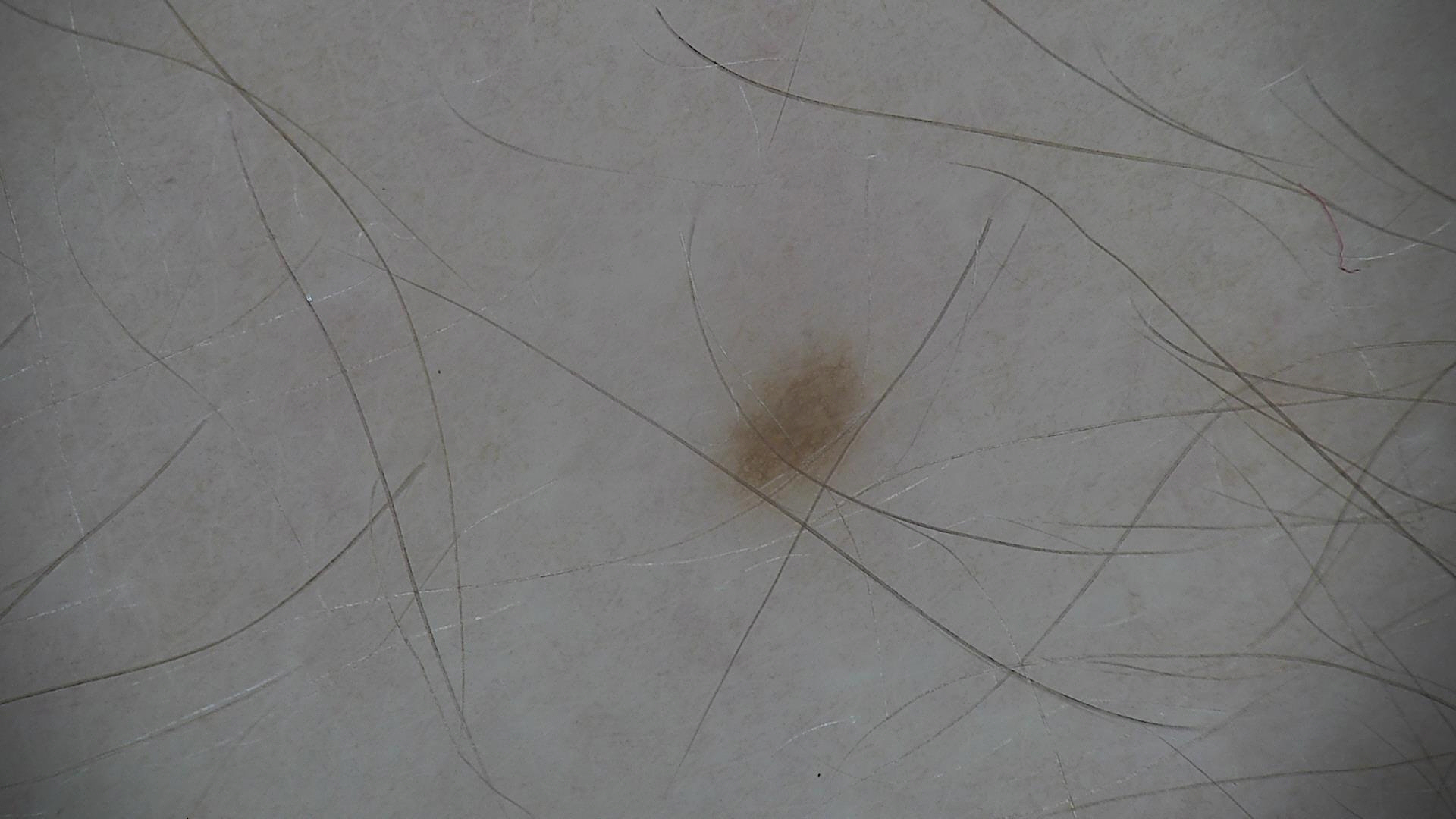The diagnosis was a junctional nevus.